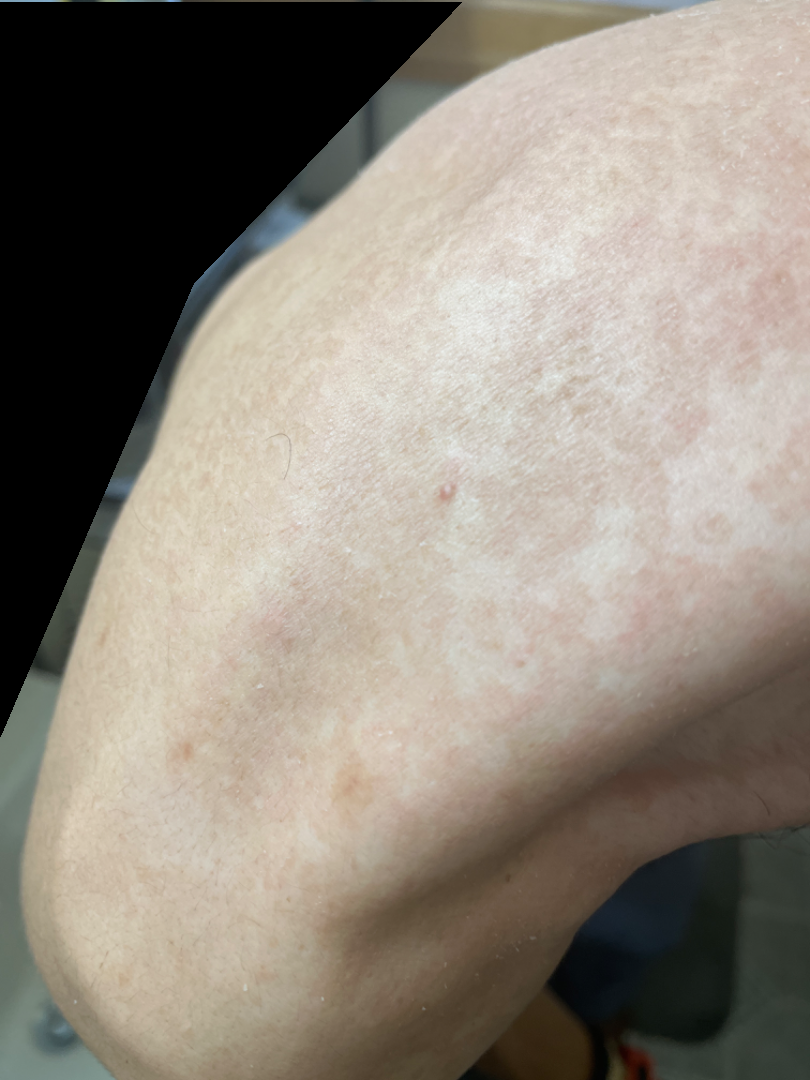| feature | finding |
|---|---|
| diagnostic considerations | the primary impression is Tinea Versicolor; less likely is Psoriasis; lower on the differential is Pityriasis rubra pilaris; less probable is Tinea |